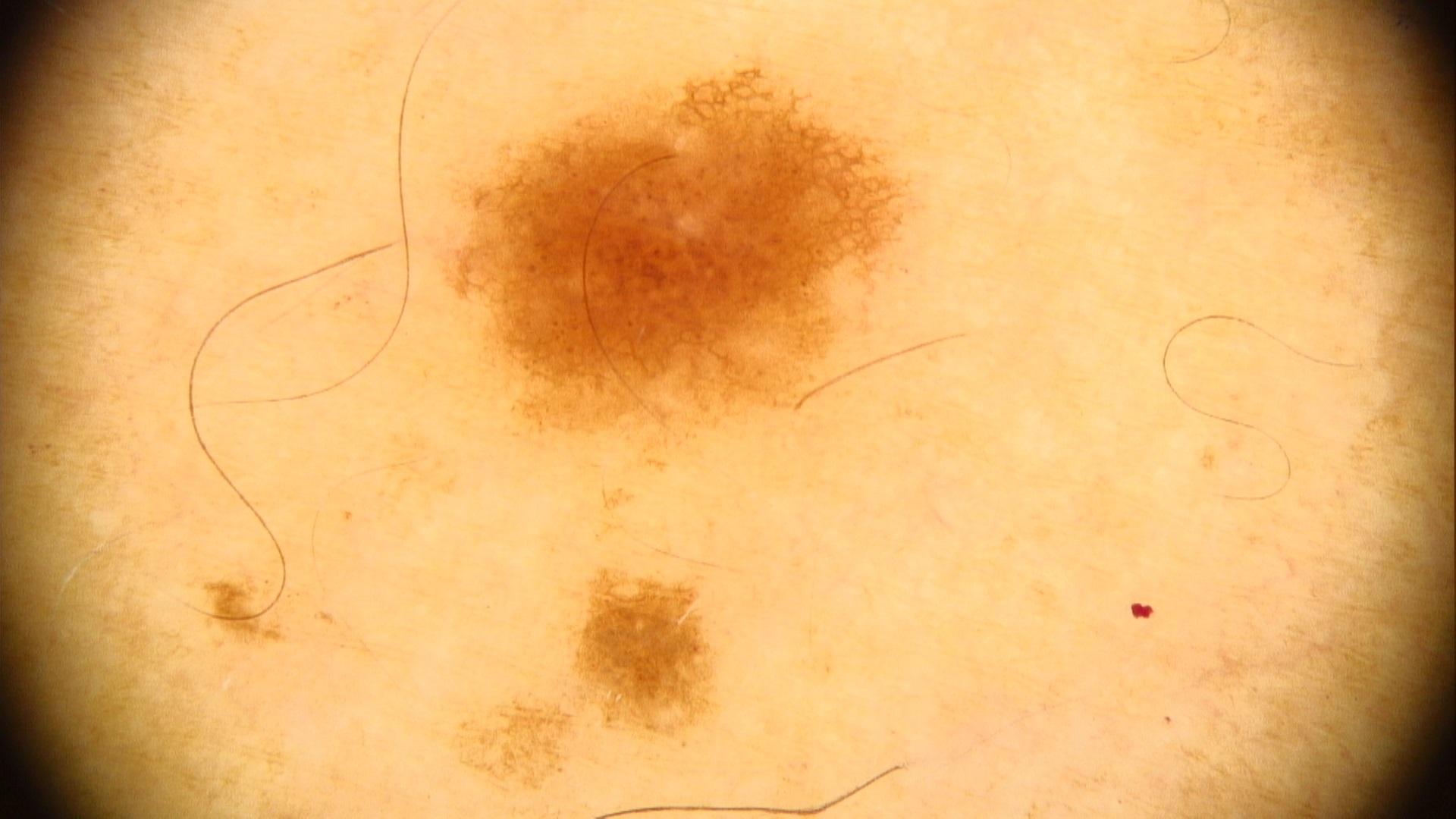{"diagnosis": {"name": "Nevus", "malignancy": "benign", "confirmation": "expert clinical impression", "lineage": "melanocytic"}}